Female subject, age 18–29; the photograph was taken at an angle; located on the head or neck — 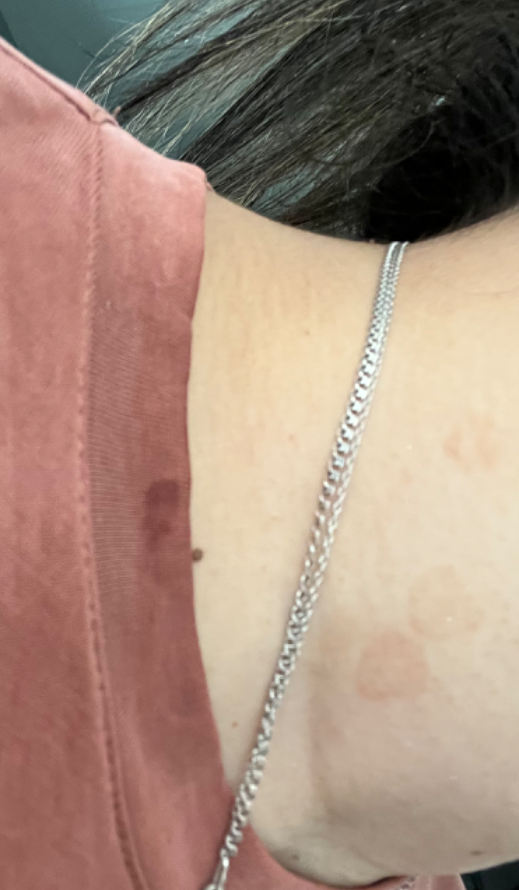Self-categorized by the patient as a rash.
Texture is reported as raised or bumpy.
The patient reported no systemic symptoms.
The patient did not report lesion symptoms.
Reported duration is about one day.
On remote review of the image: the leading impression is Tinea Versicolor.